A dermoscopic close-up of a skin lesion.
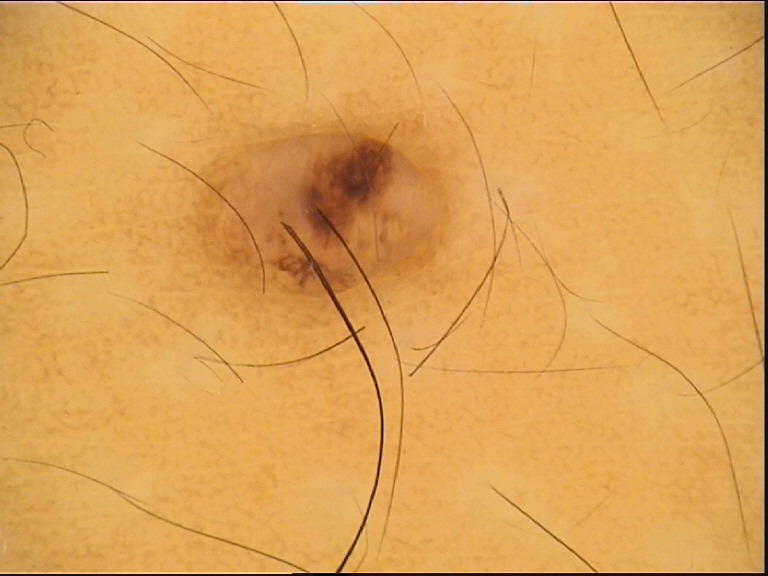Findings:
– lesion type · banal
– assessment · dermal nevus (expert consensus)